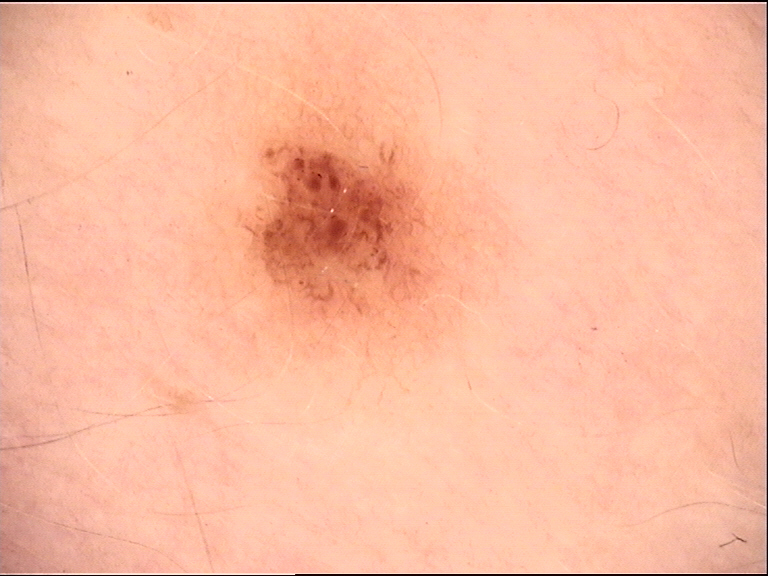{
  "image": "dermatoscopy",
  "diagnosis": {
    "name": "junctional nevus",
    "code": "jb",
    "malignancy": "benign",
    "super_class": "melanocytic",
    "confirmation": "expert consensus"
  }
}